A dermatoscopic image of a skin lesion: 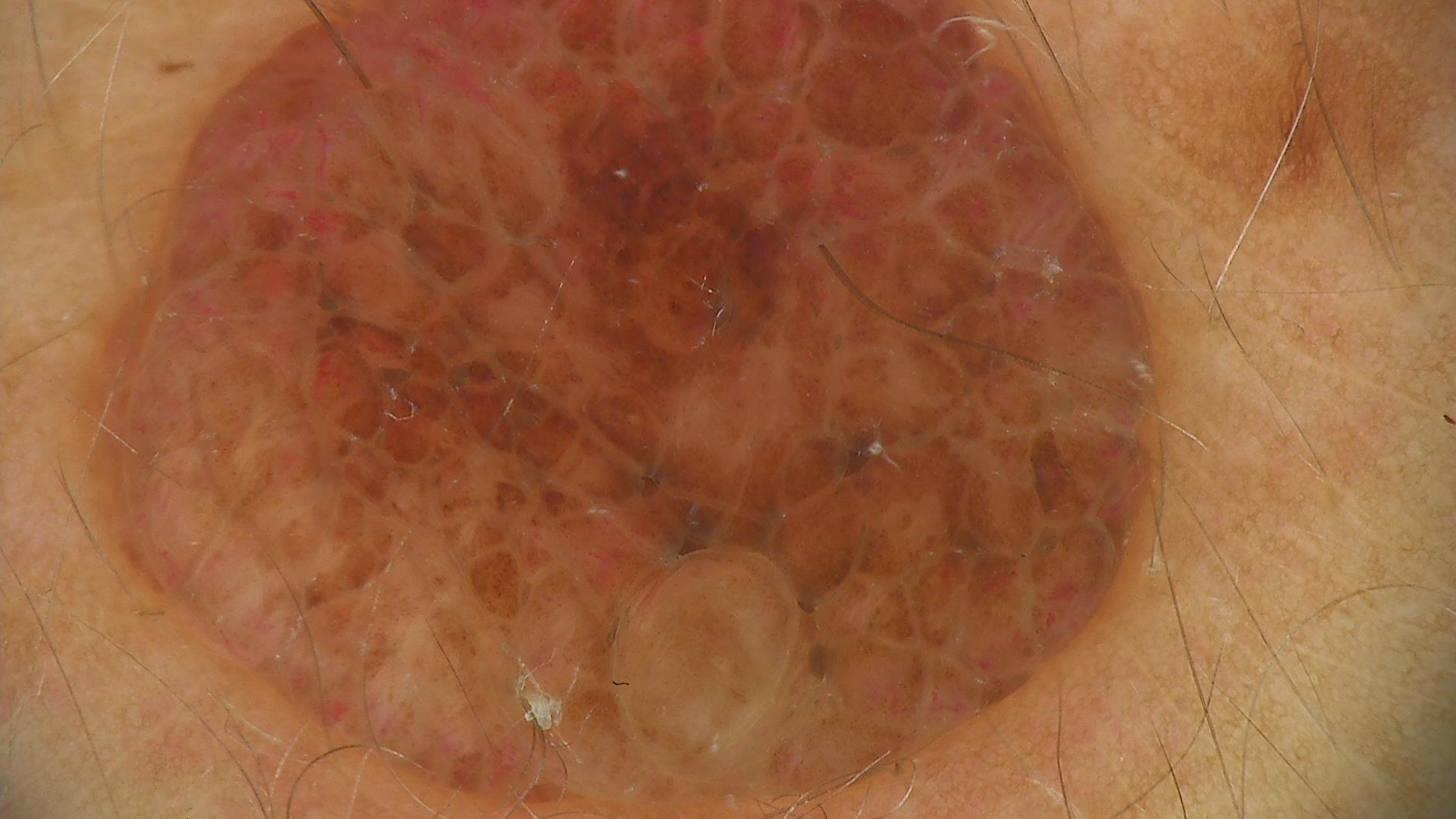This is a banal lesion.
Diagnosed as a dermal nevus.